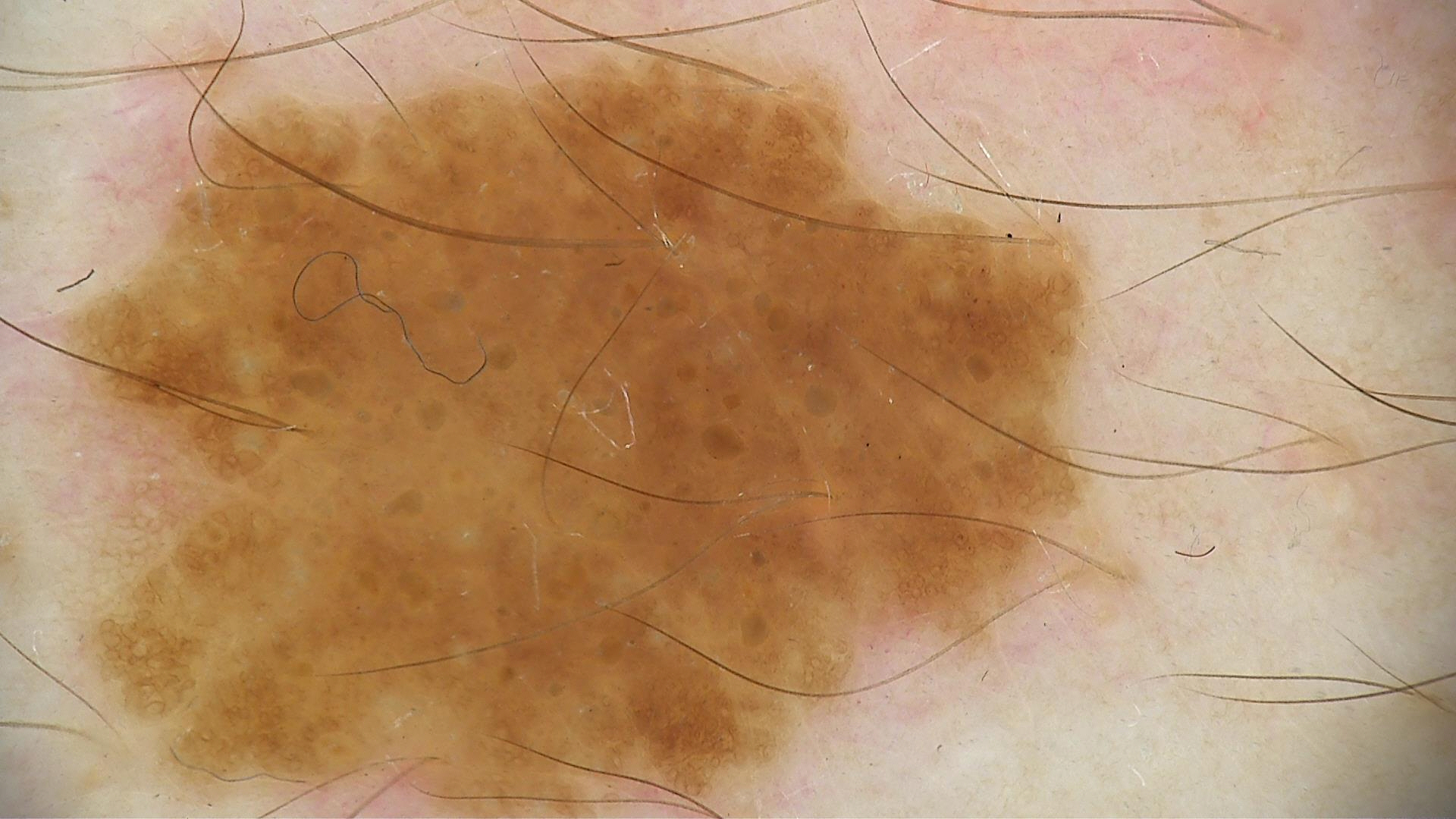The diagnostic label was a benign lesion — a dysplastic junctional nevus.